Dermoscopy of a skin lesion:
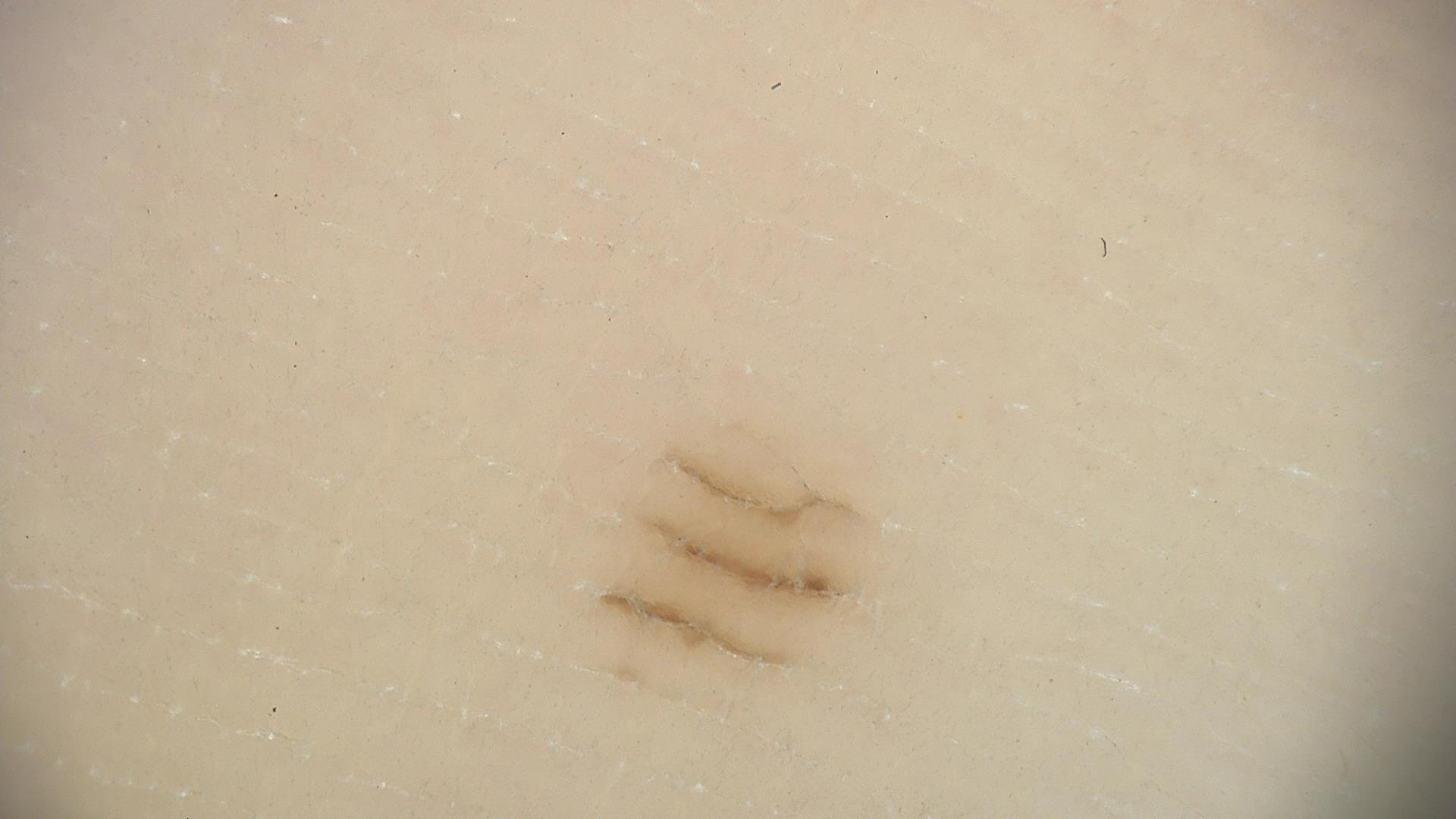Conclusion:
The diagnostic label was a benign lesion — an acral dysplastic junctional nevus.